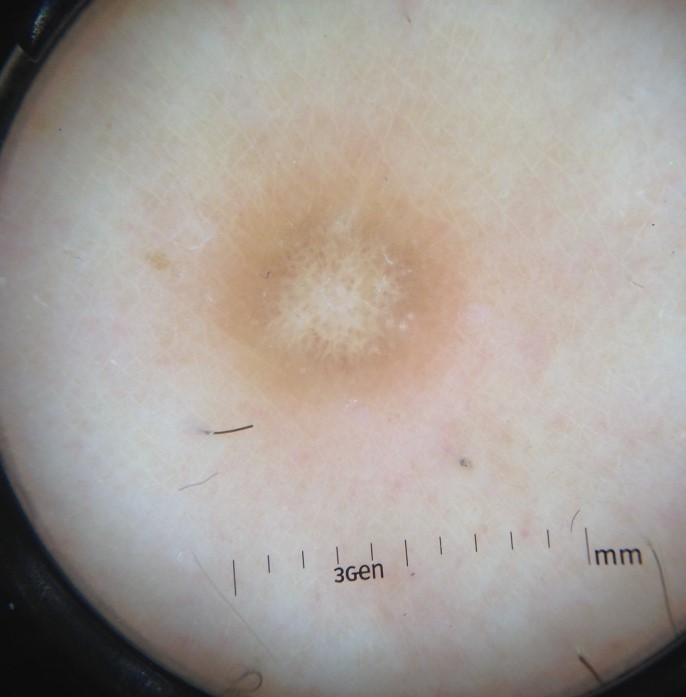Diagnosed as a dermatofibroma.